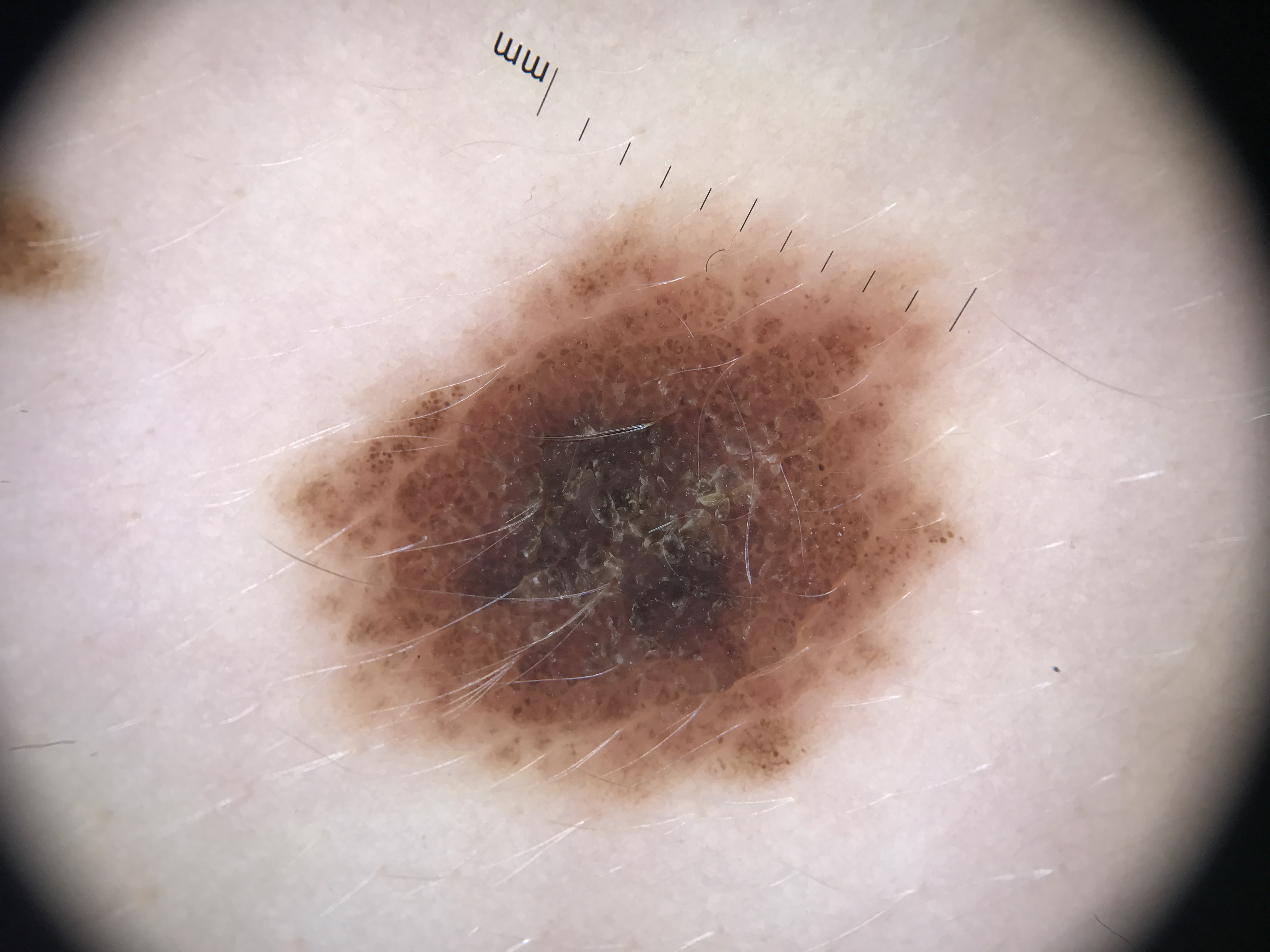Impression: Labeled as a dysplastic compound nevus.